A female patient, aged 63 to 67 · a dermoscopic view of a skin lesion.
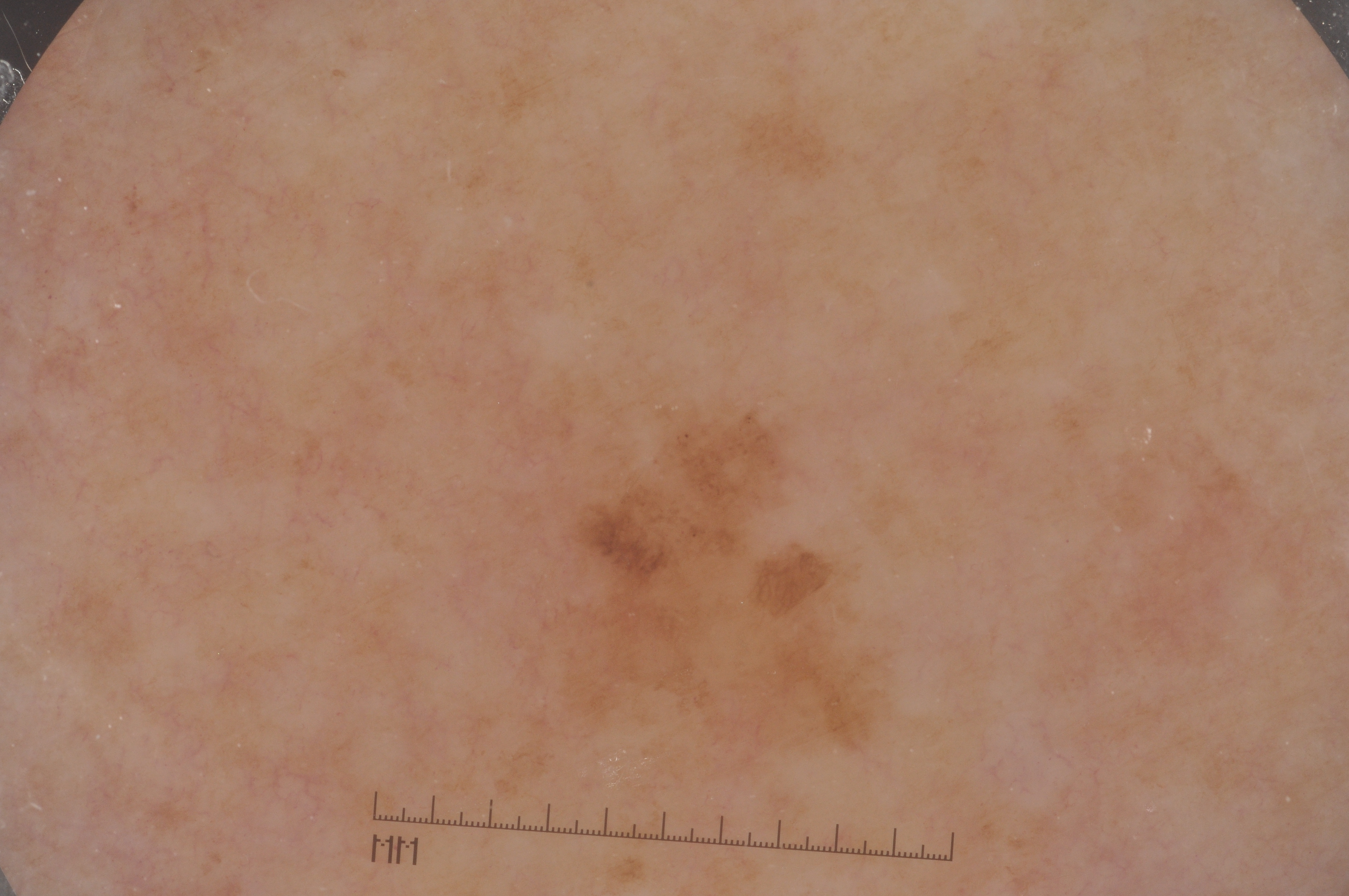The lesion occupies roughly 10% of the field. On dermoscopy, the lesion shows pigment network, with no negative network, milia-like cysts, or streaks. In (x1, y1, x2, y2) order, the lesion is located at box(519, 398, 921, 802). Expert review diagnosed this as a melanocytic nevus.